A dermatoscopic image of a skin lesion.
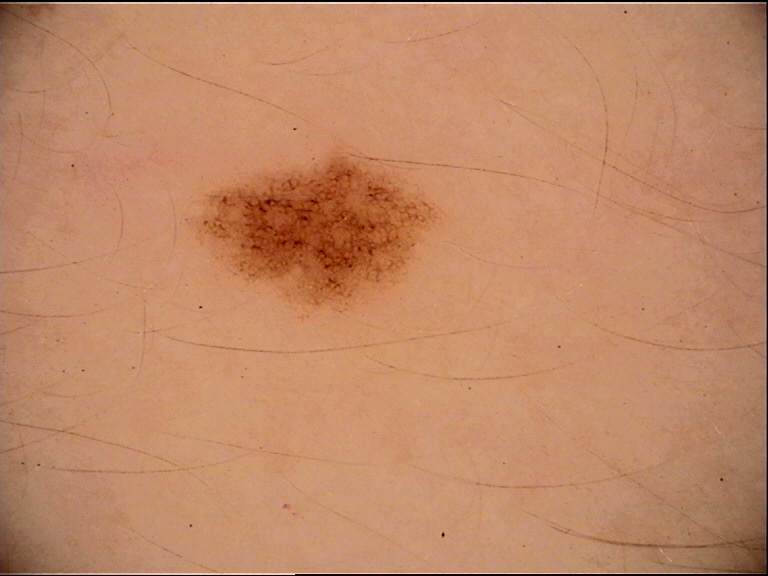Conclusion: Labeled as a dysplastic junctional nevus.